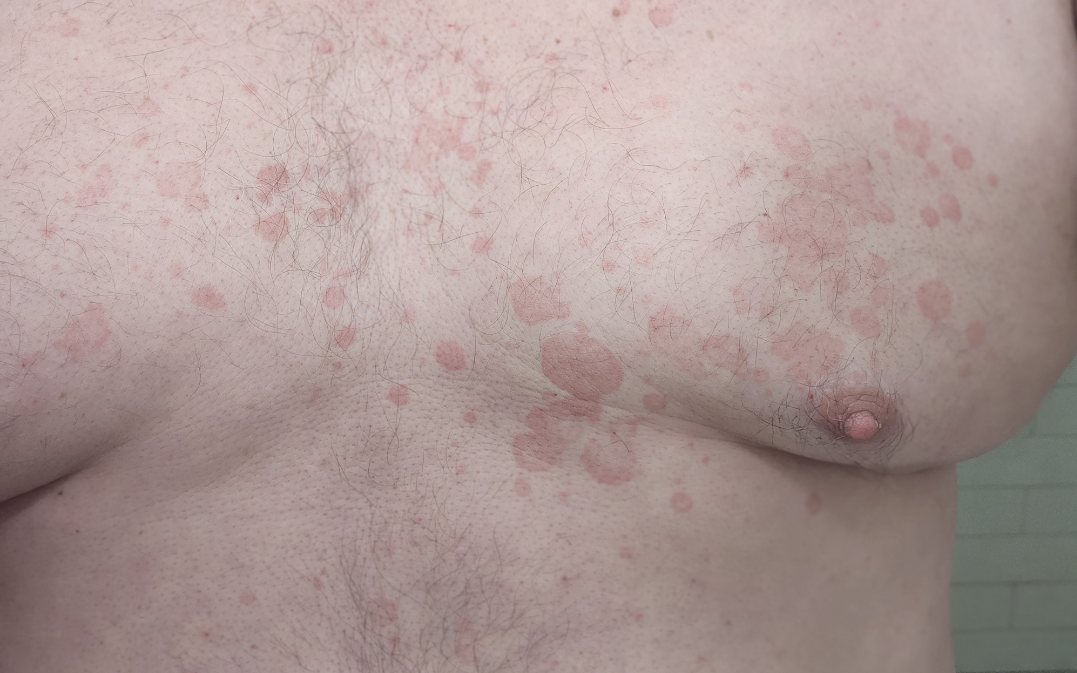| key | value |
|---|---|
| assessment | ungradable on photographic review |
| lesion texture | flat |
| patient describes the issue as | skin that appeared healthy to them |
| present for | more than one year |
| constitutional symptoms | joint pain and fatigue |
| view | at an angle |
| anatomic site | front of the torso |